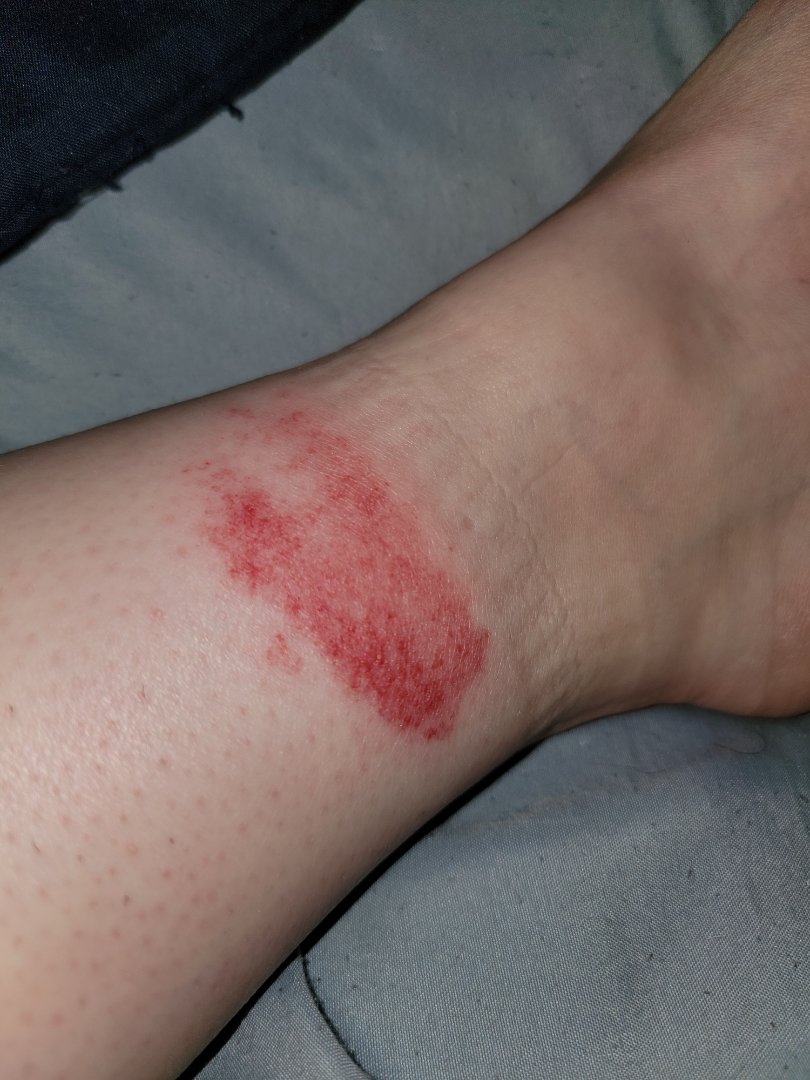On dermatologist assessment of the image, the differential includes Eczema, Allergic Contact Dermatitis and Irritant Contact Dermatitis, with no clear leading consideration.